A close-up photograph. The leg, arm, back of the torso and front of the torso are involved:
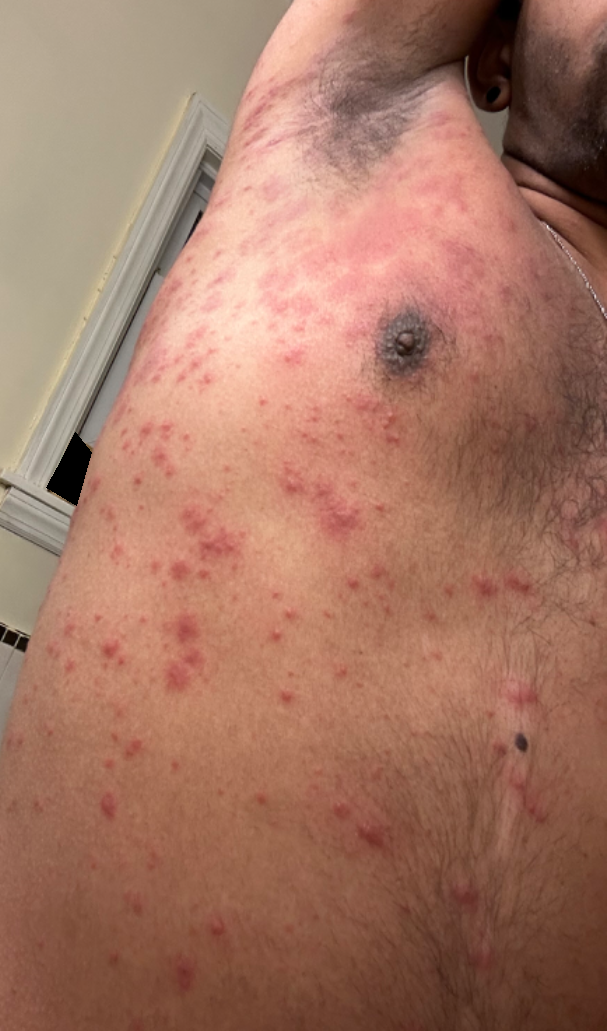Case summary:
* texture · raised or bumpy
* reported symptoms · itching, burning and enlargement
* patient's own categorization · a rash
* diagnostic considerations · Drug Rash (leading); Viral Exanthem (remote); Scabies (remote); Folliculitis (remote); Allergic Contact Dermatitis (remote)